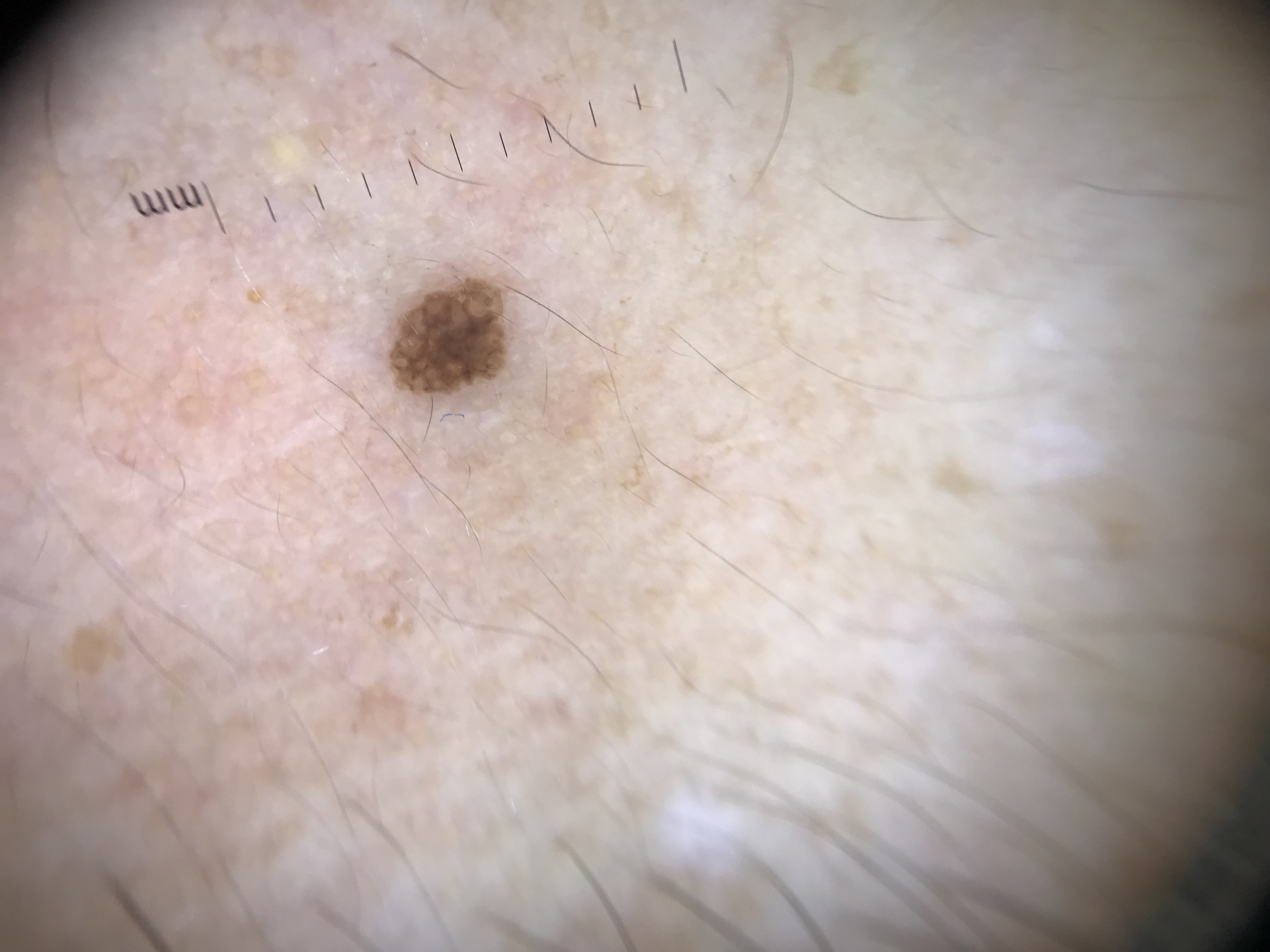modality: dermatoscopy, subtype: keratinocytic, label: seborrheic keratosis (expert consensus).